A dermoscopic photograph of a skin lesion: 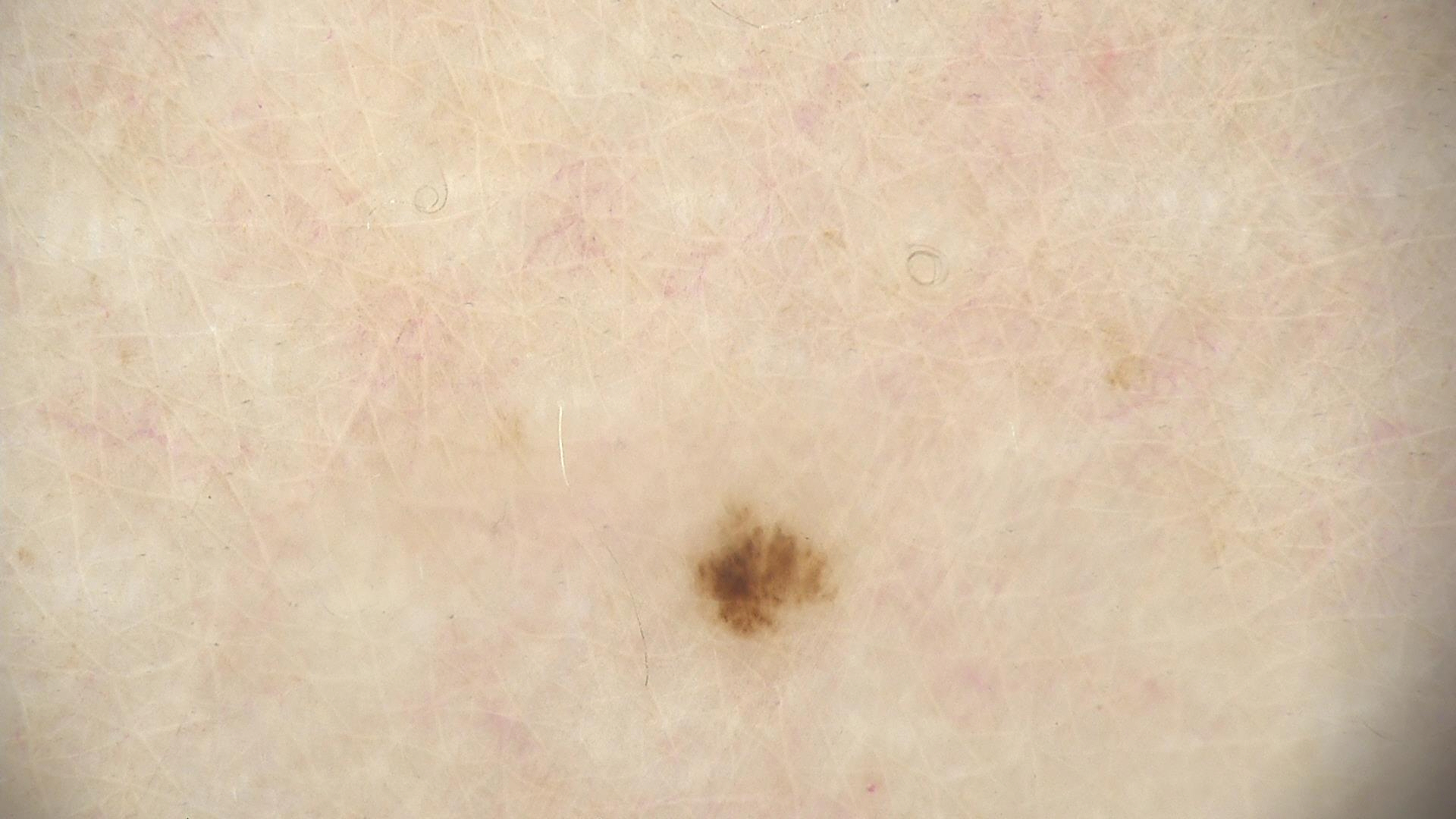The diagnosis was a dysplastic junctional nevus.